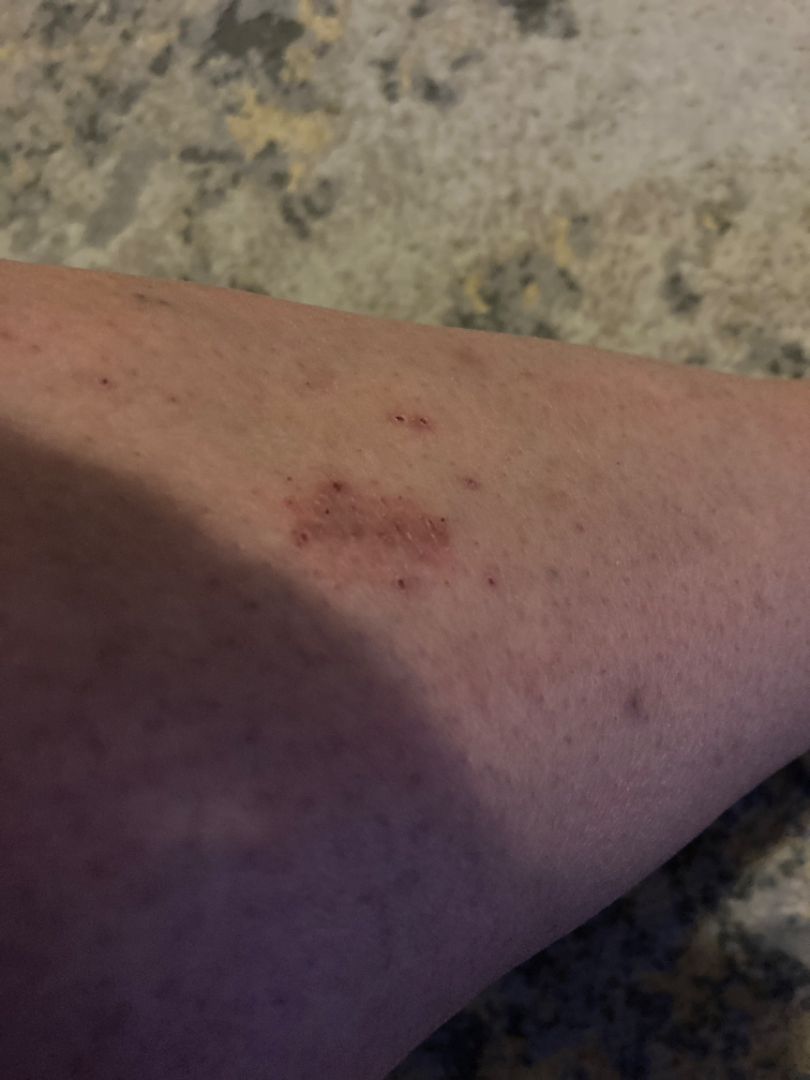The patient indicates the lesion is rough or flaky. Present for one to three months. The lesion is associated with itching. The patient indicates associated joint pain. The subject is a female aged 50–59. Located on the leg and arm. The photo was captured at an angle. On photographic review, the primary impression is Eczema; an alternative is Psoriasis; the differential also includes Allergic Contact Dermatitis; less likely is Tinea.